Dermoscopy of a skin lesion: 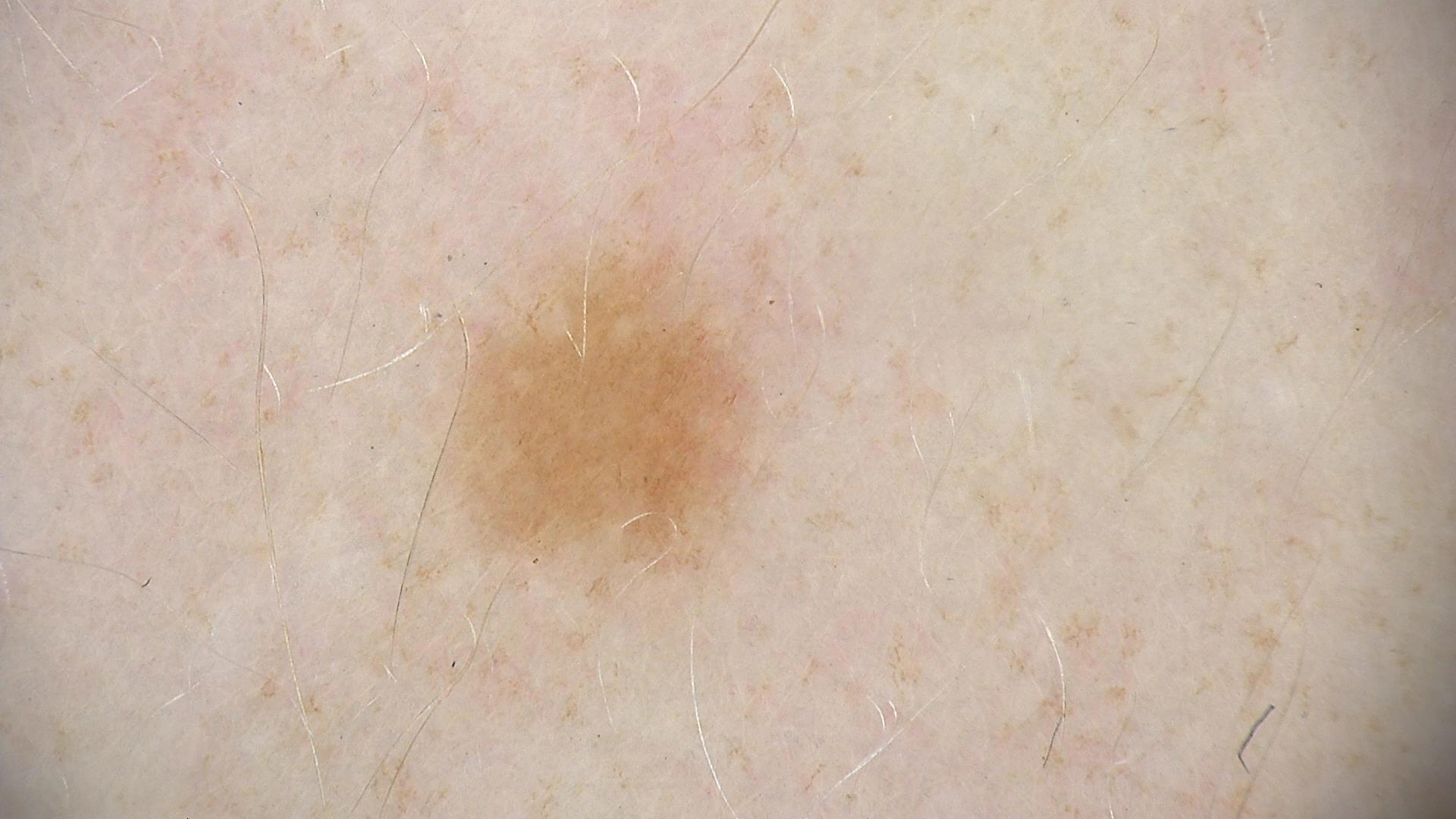label: dysplastic junctional nevus (expert consensus)